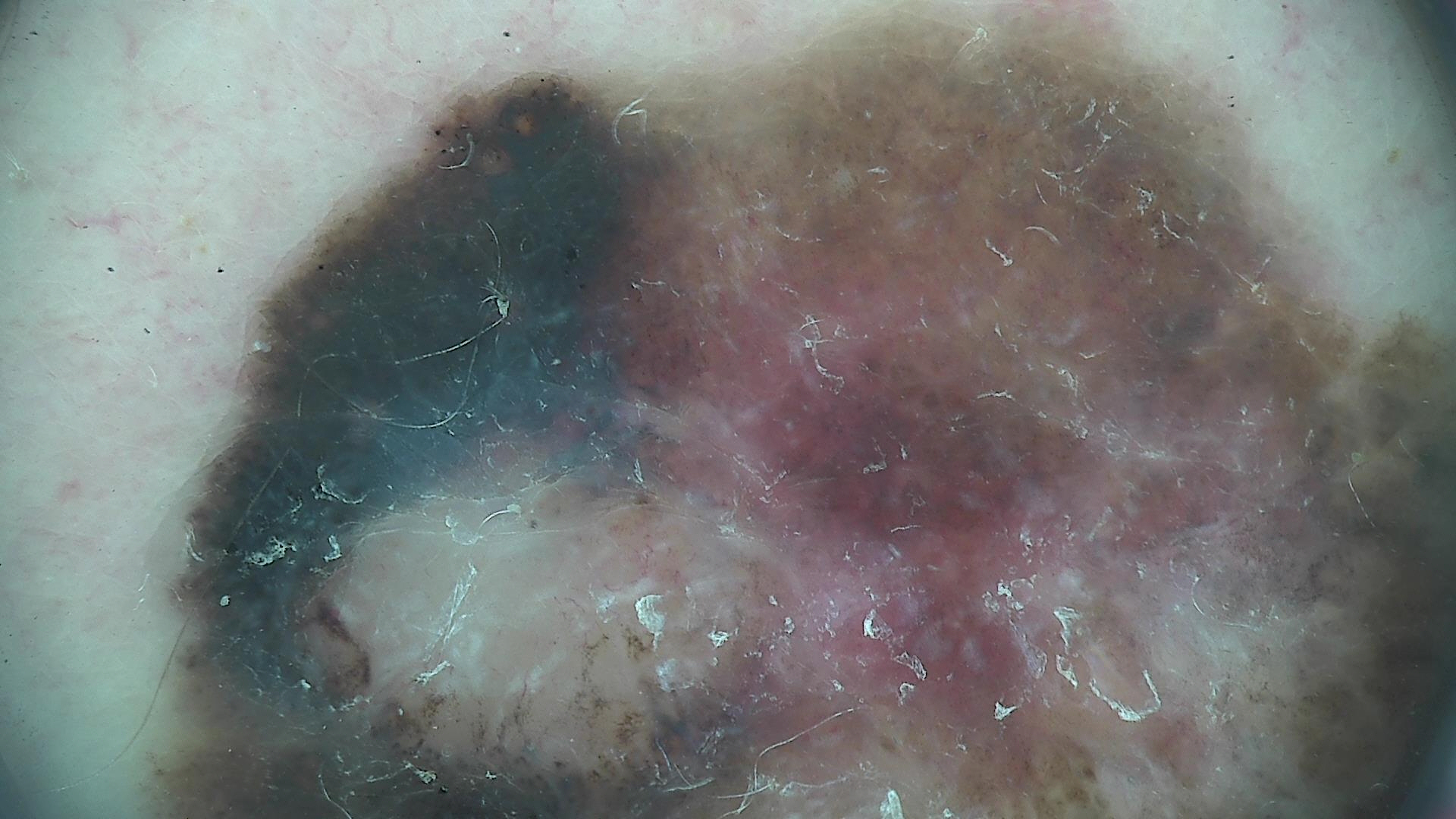Conclusion: Biopsy-confirmed as a melanoma.